A dermoscopic close-up of a skin lesion. The subject is a male aged 43 to 47: 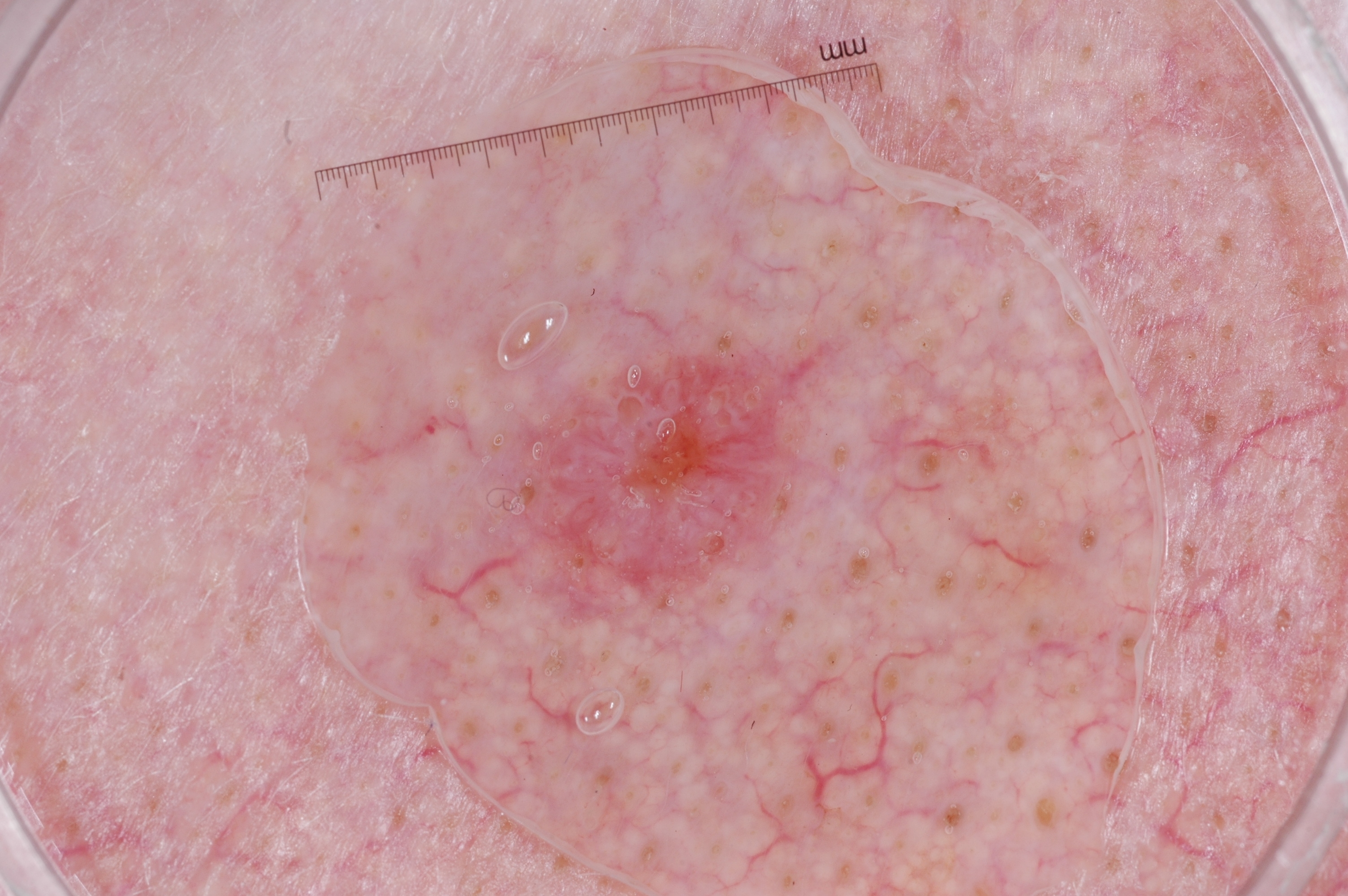In (x1, y1, x2, y2) order, the lesion's extent is 486, 310, 843, 626.
The dermoscopic pattern shows no streaks, milia-like cysts, pigment network, or negative network.
The diagnostic assessment was a melanocytic nevus.